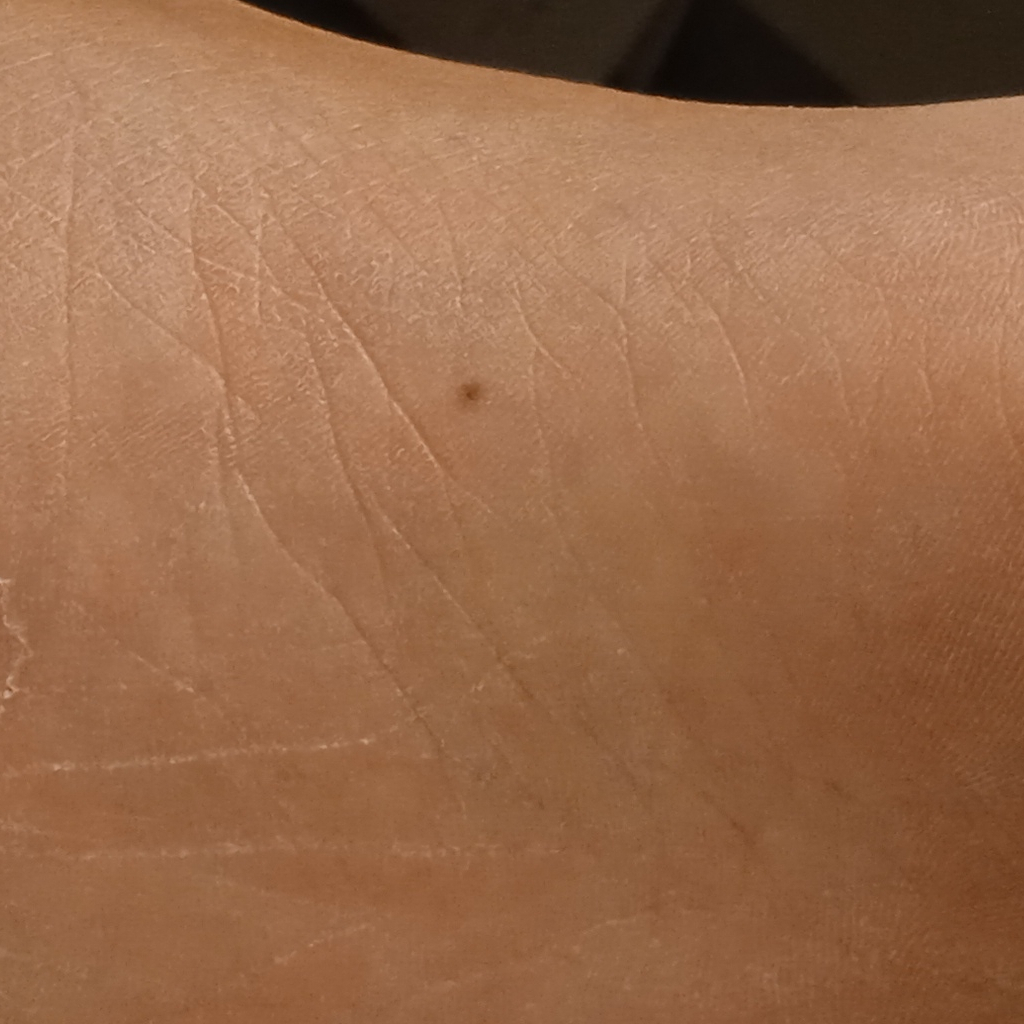Case summary: A clinical photograph showing a skin lesion. Acquired for a research image collection, with no referral diagnosis. By self-report, a personal history of cancer. The lesion is located on a leg. The lesion is about 2.2 mm across. Impression: The consensus diagnosis for this lesion was a melanocytic nevus.